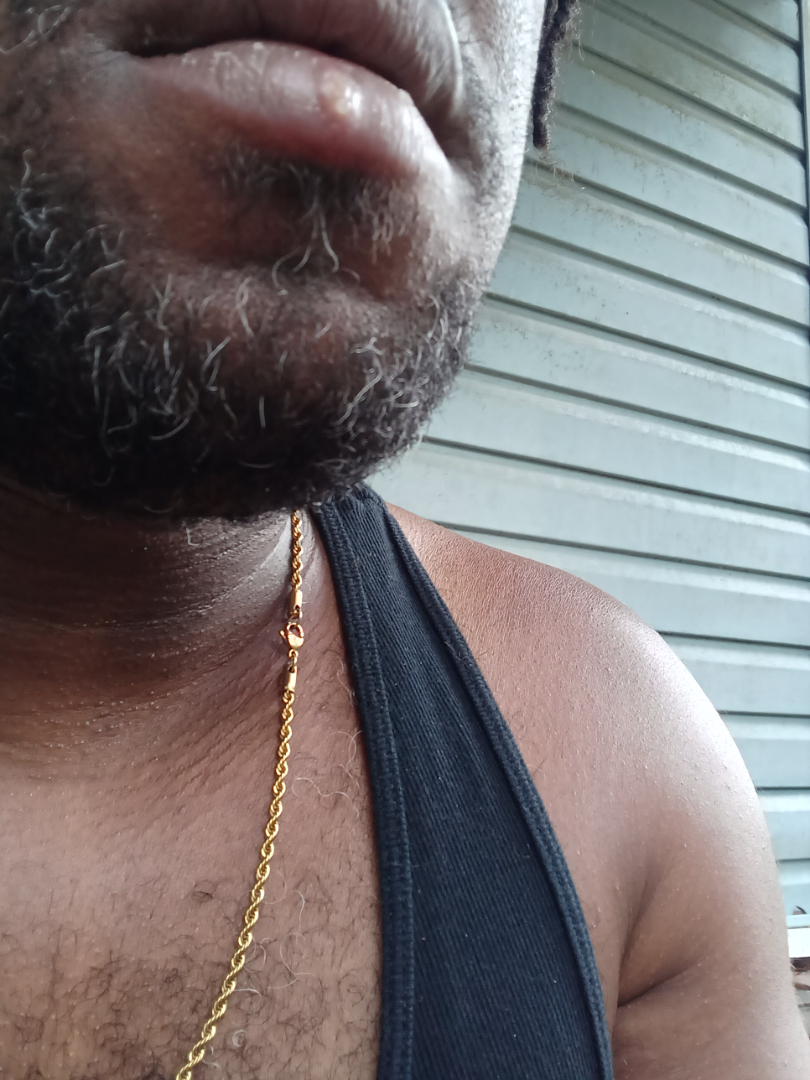Q: What was the assessment?
A: no findings on review